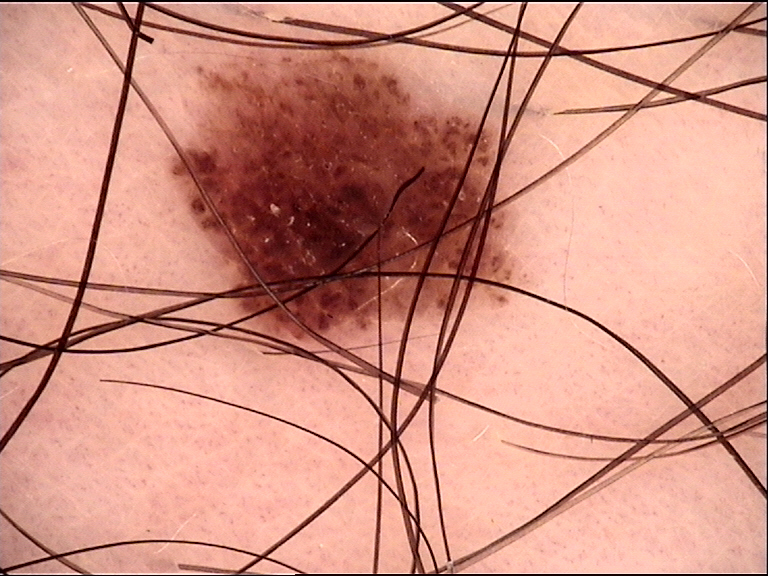Q: What is the diagnosis?
A: dysplastic junctional nevus (expert consensus)